The leg is involved; the condition has been present for less than one week; the patient notes darkening, enlargement, burning and bothersome appearance; the photograph is a close-up of the affected area; the lesion is described as flat:
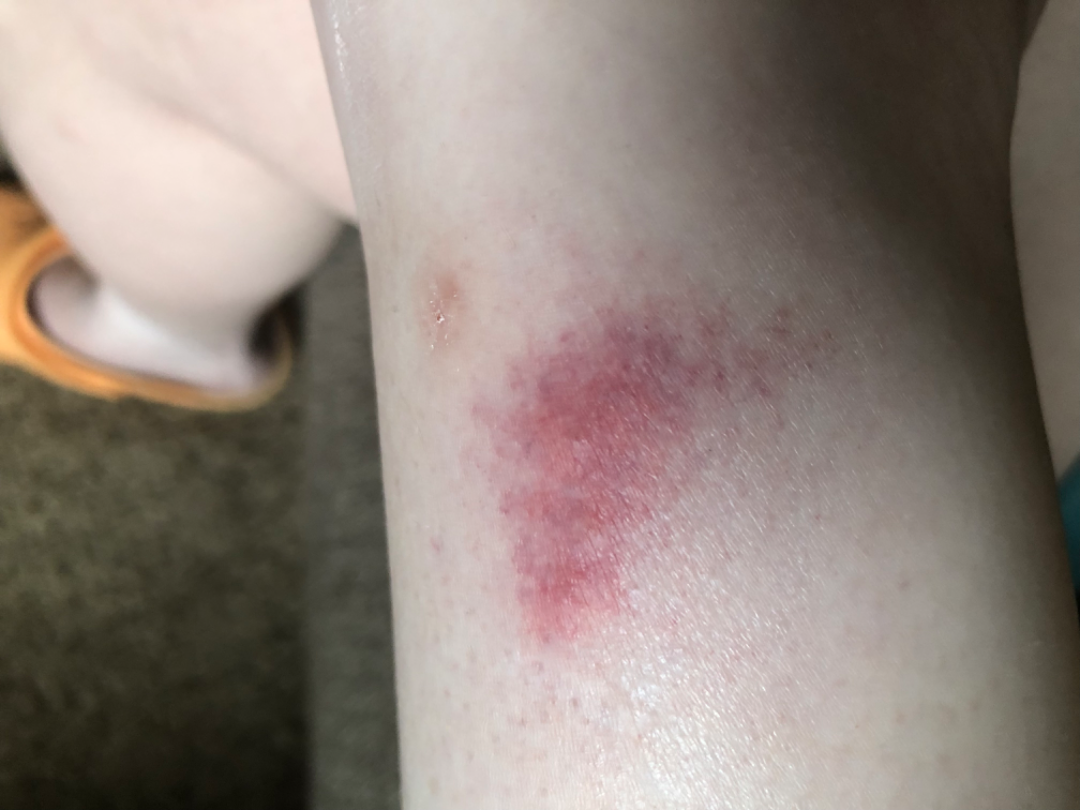Impression: On dermatologist assessment of the image: the impression was split between Pigmented purpuric eruption and Eczema.